A dermoscopic image of a skin lesion:
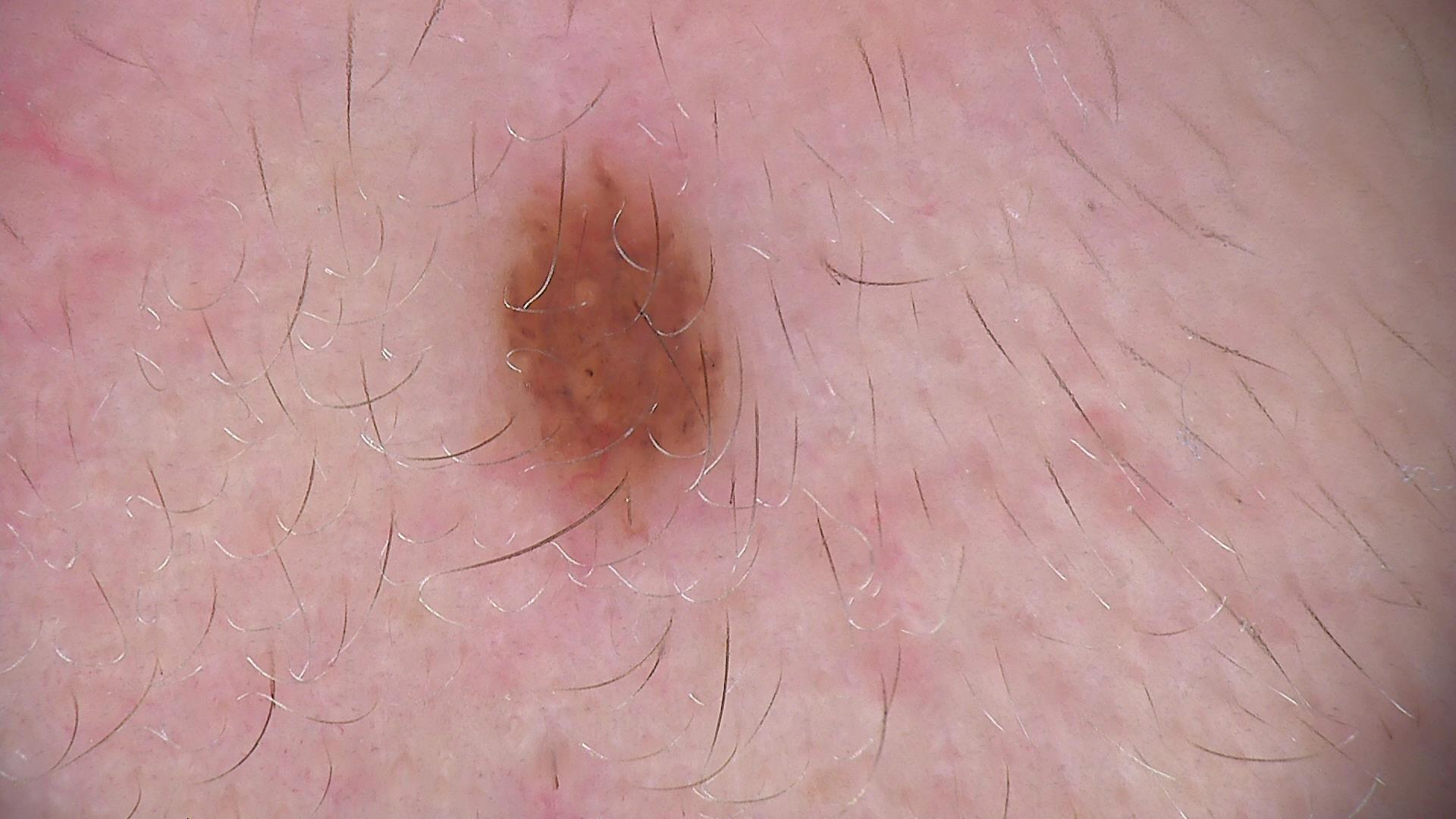The diagnosis was a benign lesion — a dysplastic junctional nevus.